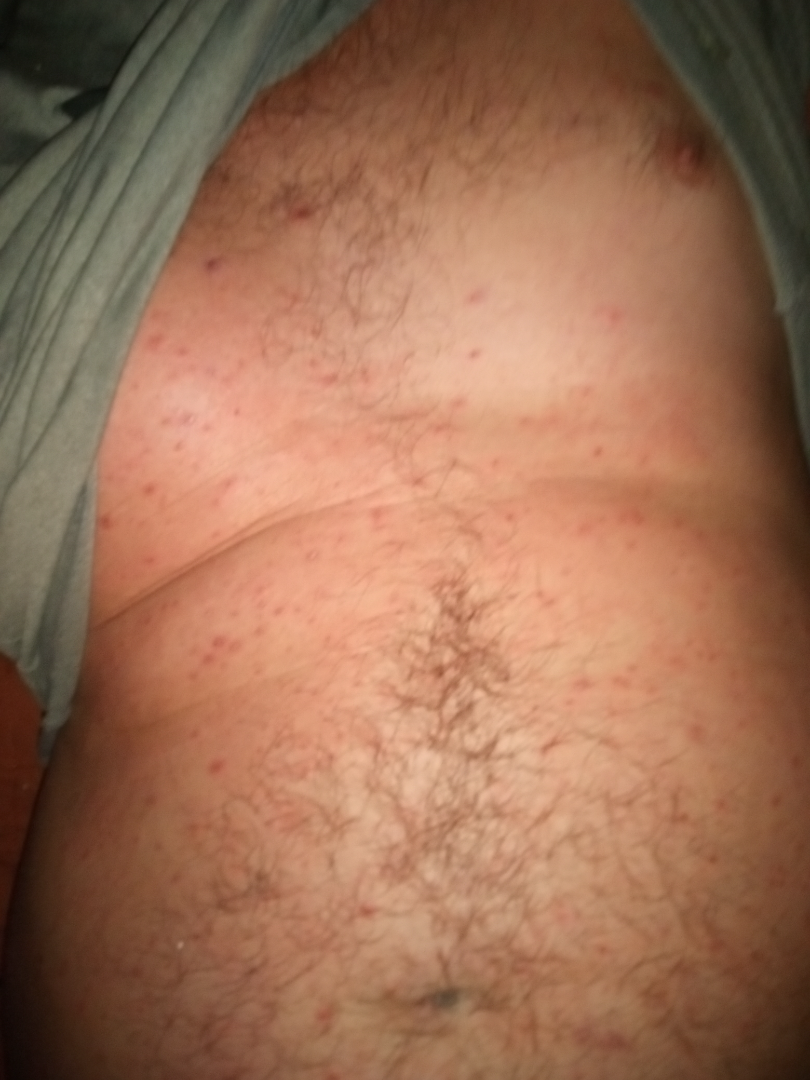Case summary:
– self-categorized as — a rash
– view — at a distance
– surface texture — rough or flaky and raised or bumpy
– subject — male, age 40–49
– history — one to four weeks
– location — front of the torso and leg
– differential — Scabies (29%); Grover's disease (18%); Folliculitis (15%); Drug Rash (15%); Syphilis (11%); Pityriasis lichenoides (11%)